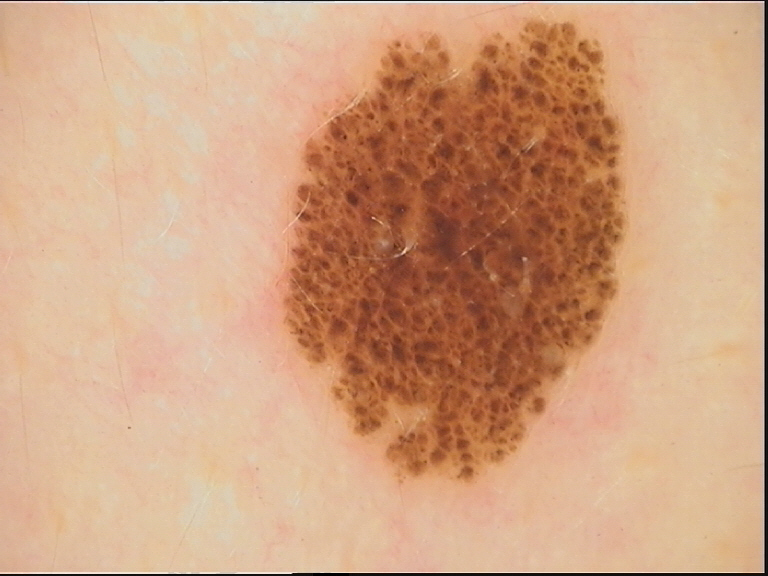Impression:
Consistent with a banal lesion — a compound nevus.